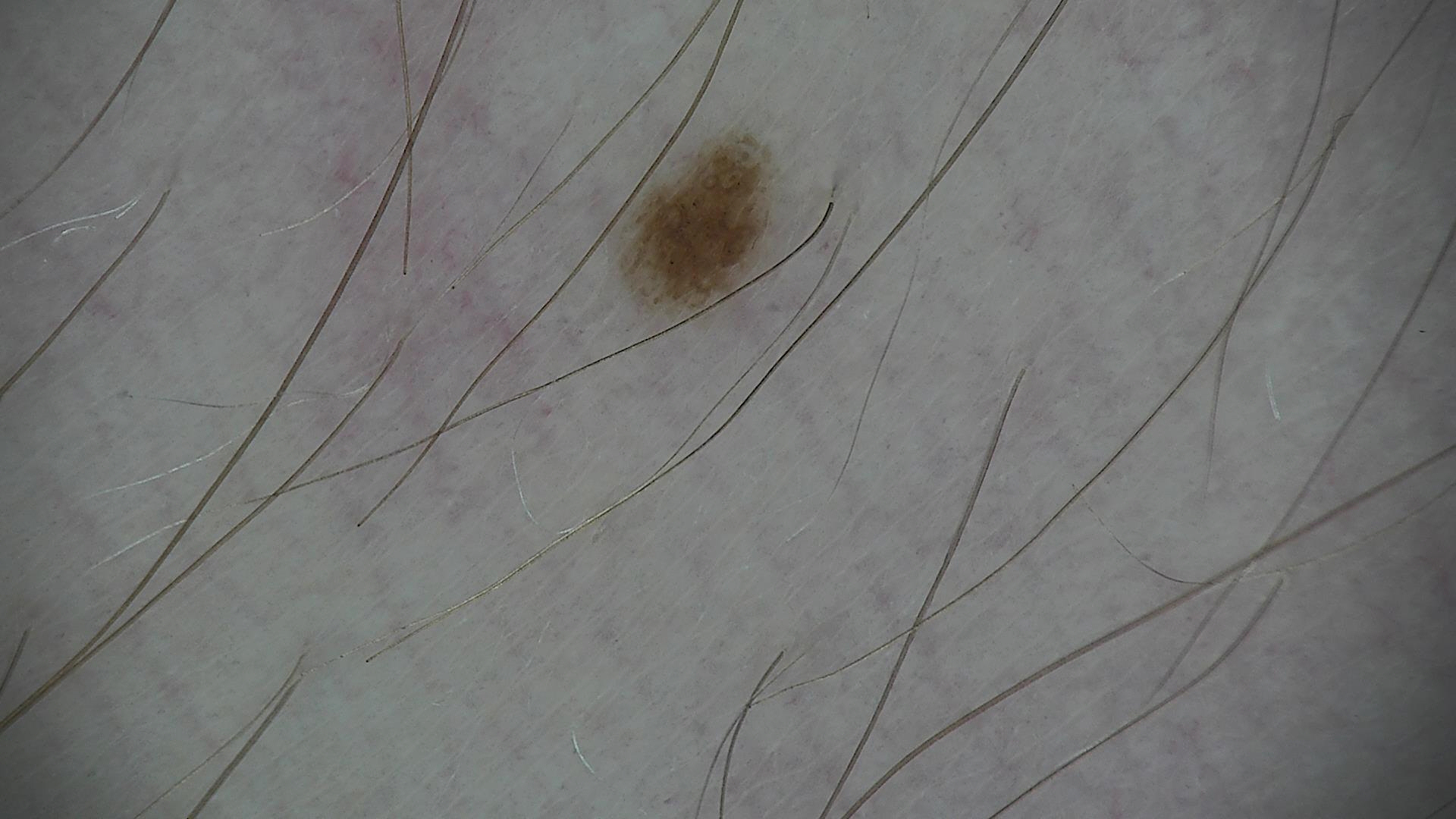A skin lesion imaged with a dermatoscope.
The diagnosis was a dysplastic junctional nevus.